A dermoscopic image of a skin lesion.
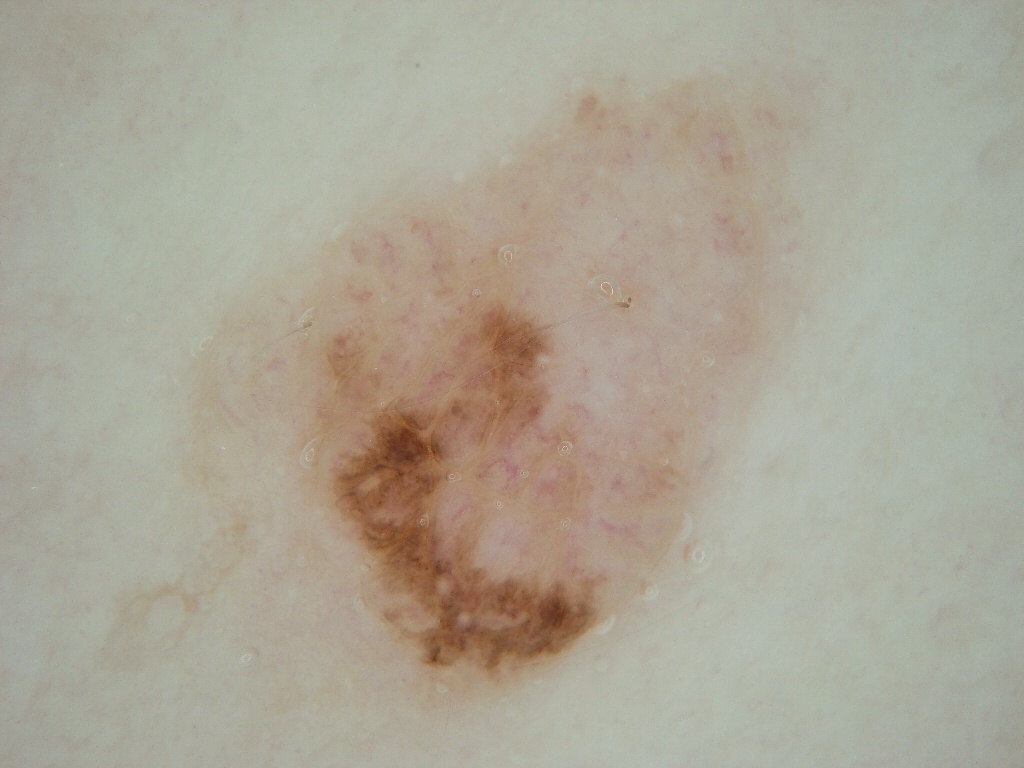absent dermoscopic features: pigment network, milia-like cysts, globules, streaks, and negative network; location: left=205, top=55, right=816, bottom=707; diagnosis: a melanocytic nevus.